A dermoscopic close-up of a skin lesion.
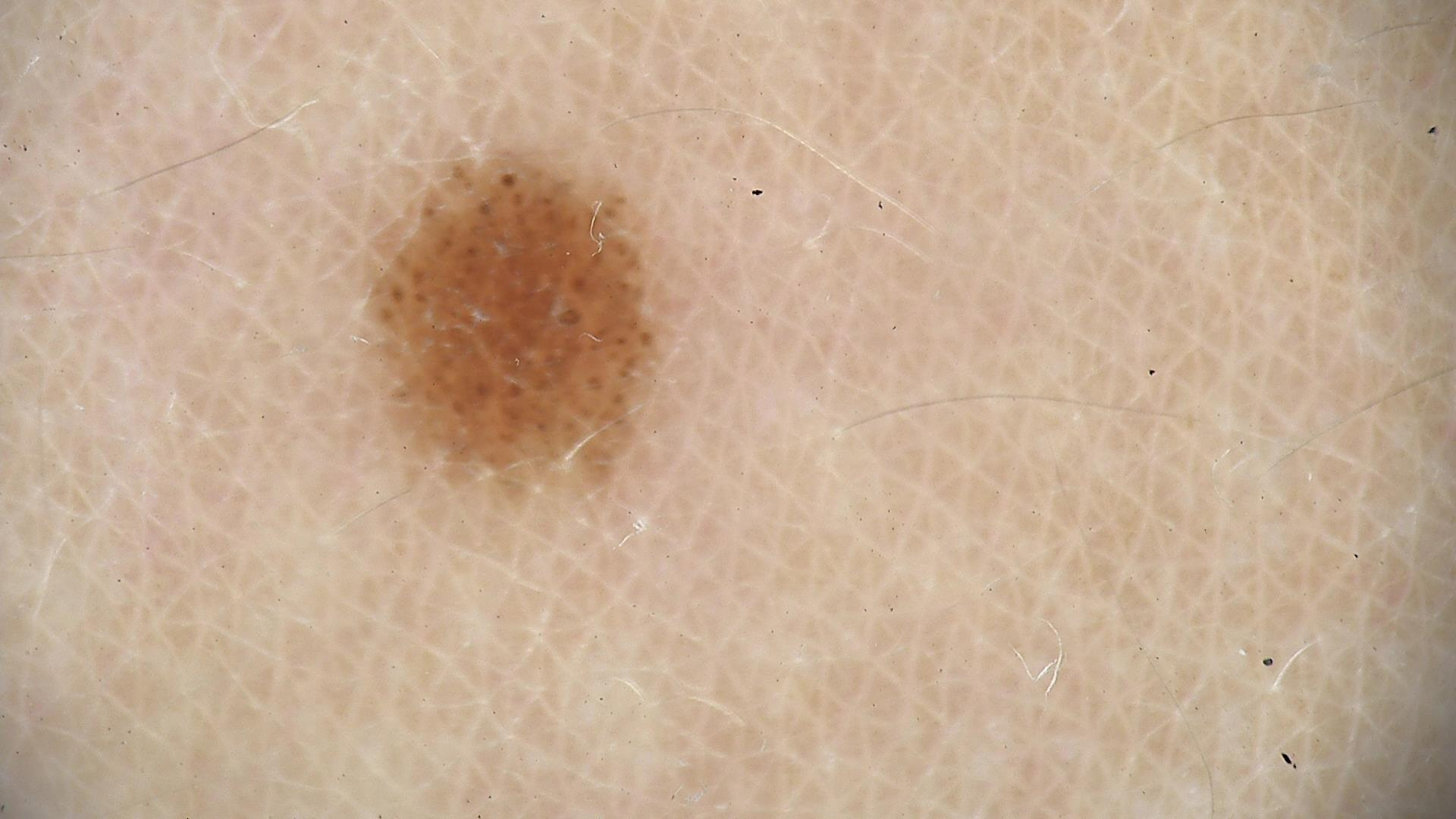Impression:
Labeled as a dysplastic junctional nevus.